The photograph is a close-up of the affected area:
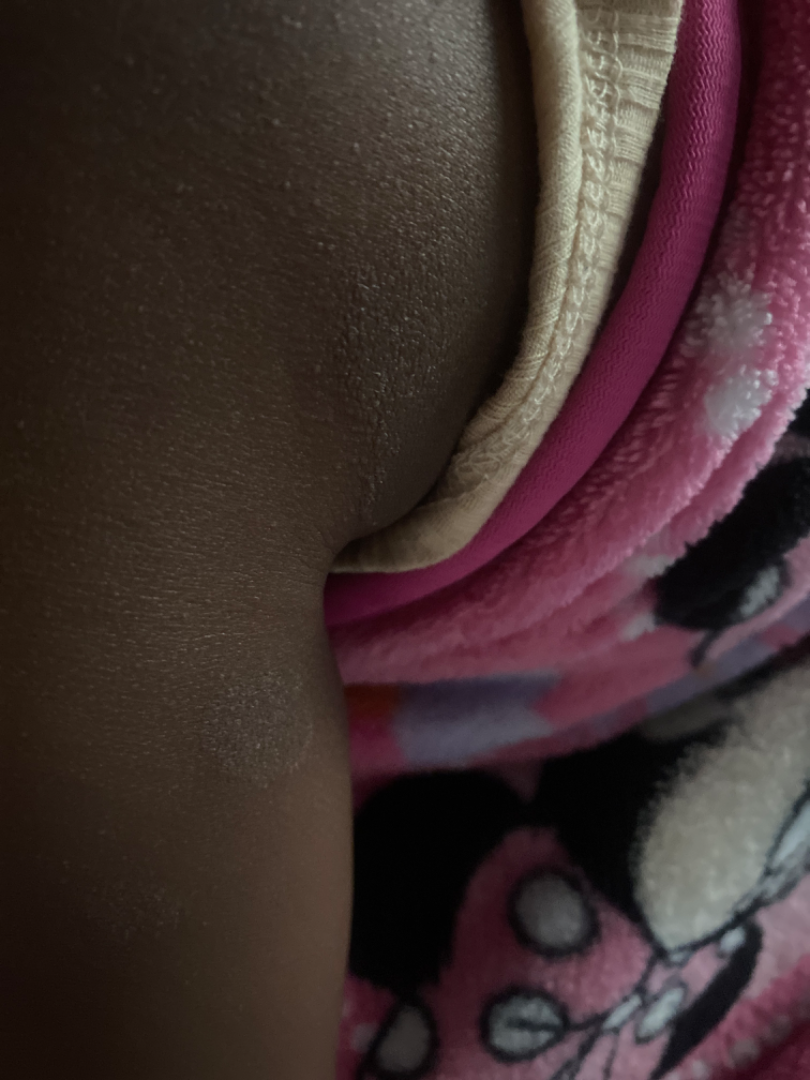The skin findings could not be characterized from the image.